A clinical photograph showing a skin lesion · a subject 81 years of age: 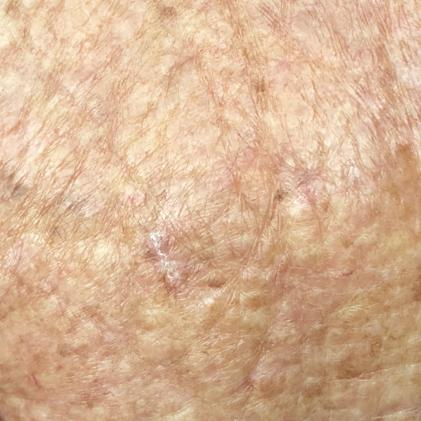<record>
  <lesion_location>the chest</lesion_location>
  <symptoms>
    <present>itching</present>
  </symptoms>
  <diagnosis>
    <name>actinic keratosis</name>
    <code>ACK</code>
    <malignancy>indeterminate</malignancy>
    <confirmation>clinical consensus</confirmation>
  </diagnosis>
</record>